The lesion involves the back of the torso, top or side of the foot, arm and leg · close-up view — 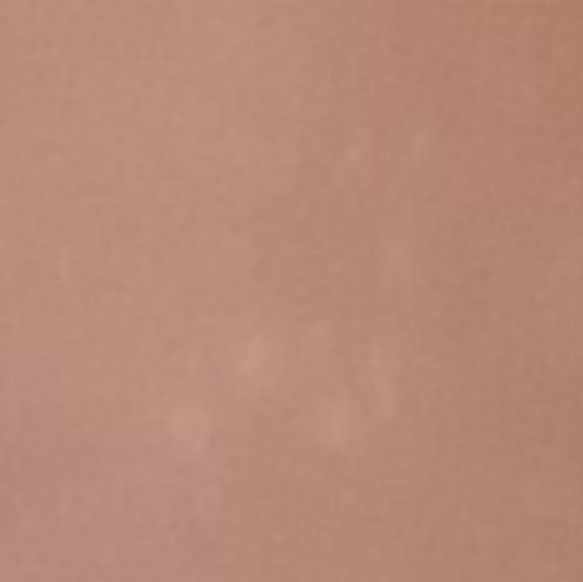The skin condition could not be confidently assessed from this image.
The patient notes itching.
Reported duration is more than one year.
The patient notes the lesion is flat.